A dermoscopic image of a skin lesion: 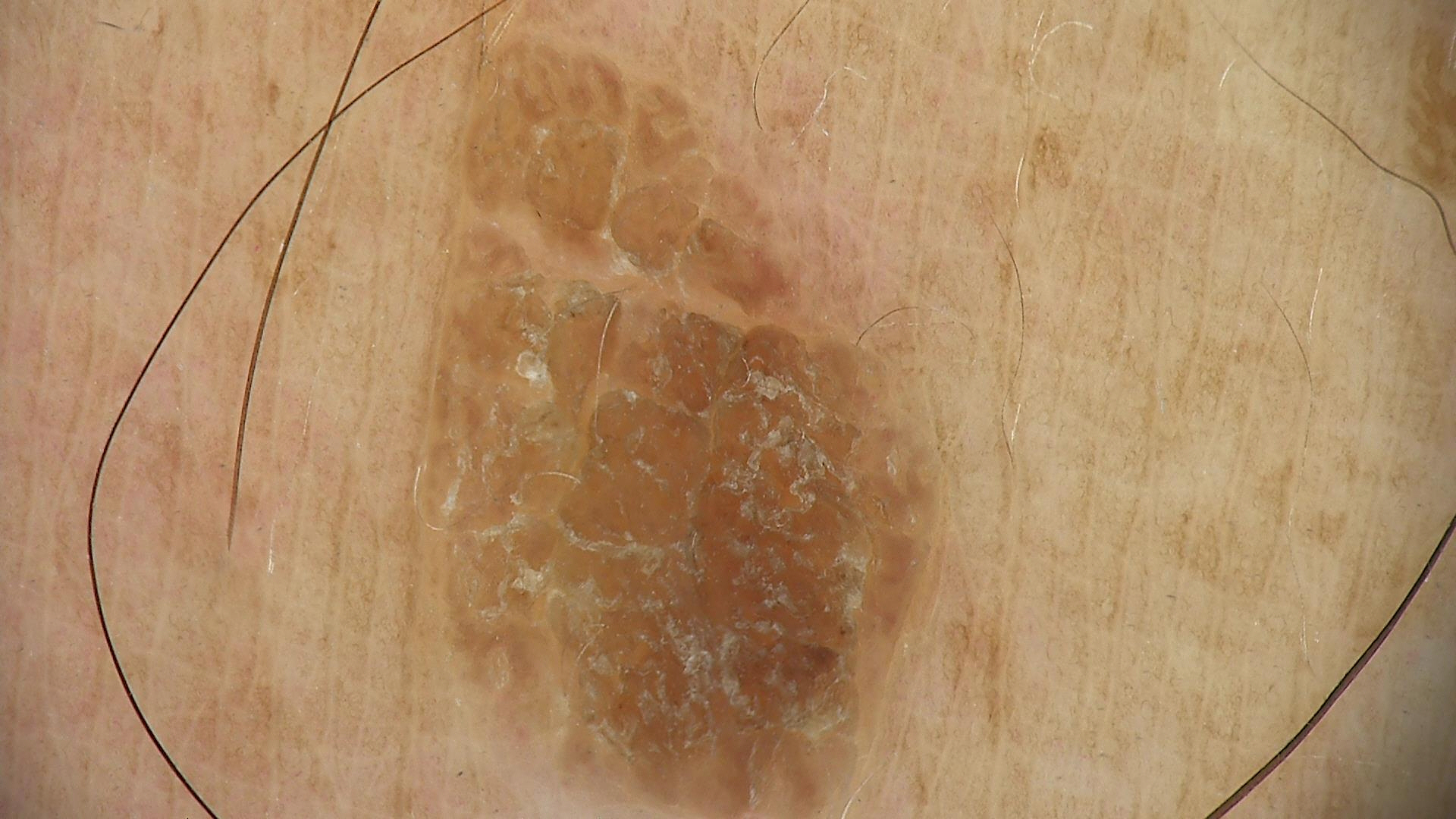Case:
* assessment: seborrheic keratosis (expert consensus)